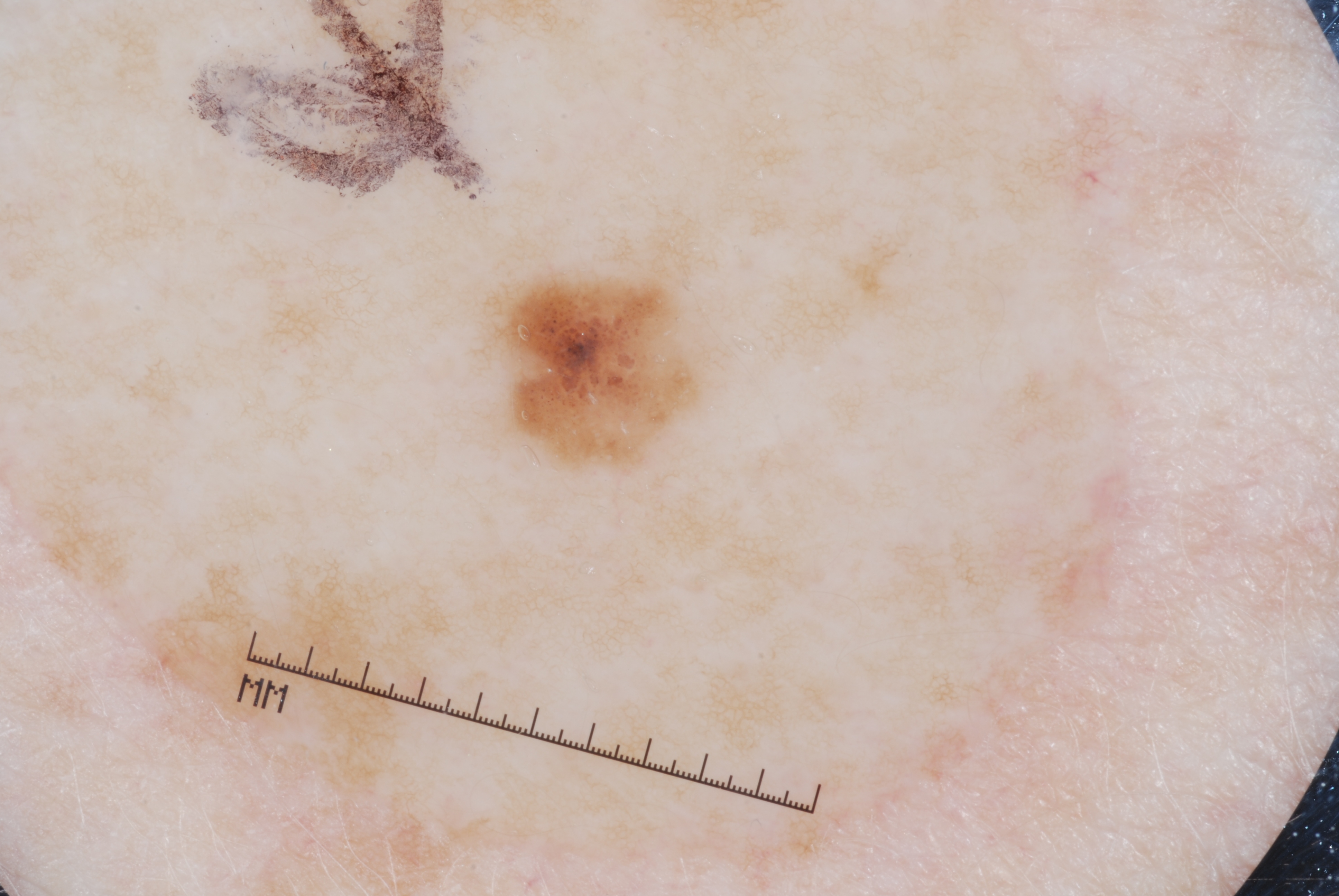Q: Who is the patient?
A: male, aged 38-42
Q: How was this image acquired?
A: dermoscopic image
Q: Which dermoscopic features were noted?
A: milia-like cysts and pigment network
Q: Where is the lesion located?
A: 491 273 701 462
Q: What is the diagnosis?
A: a melanocytic nevus